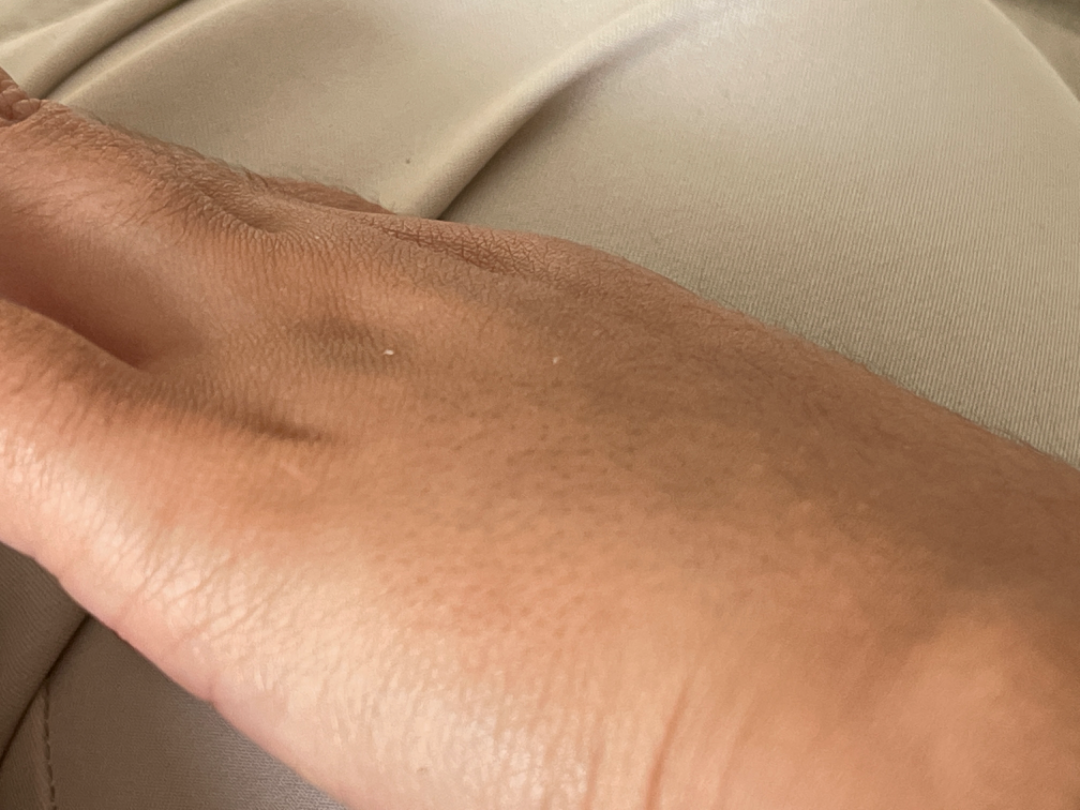assessment: indeterminate from the photograph.